A dermoscopic photograph of a skin lesion.
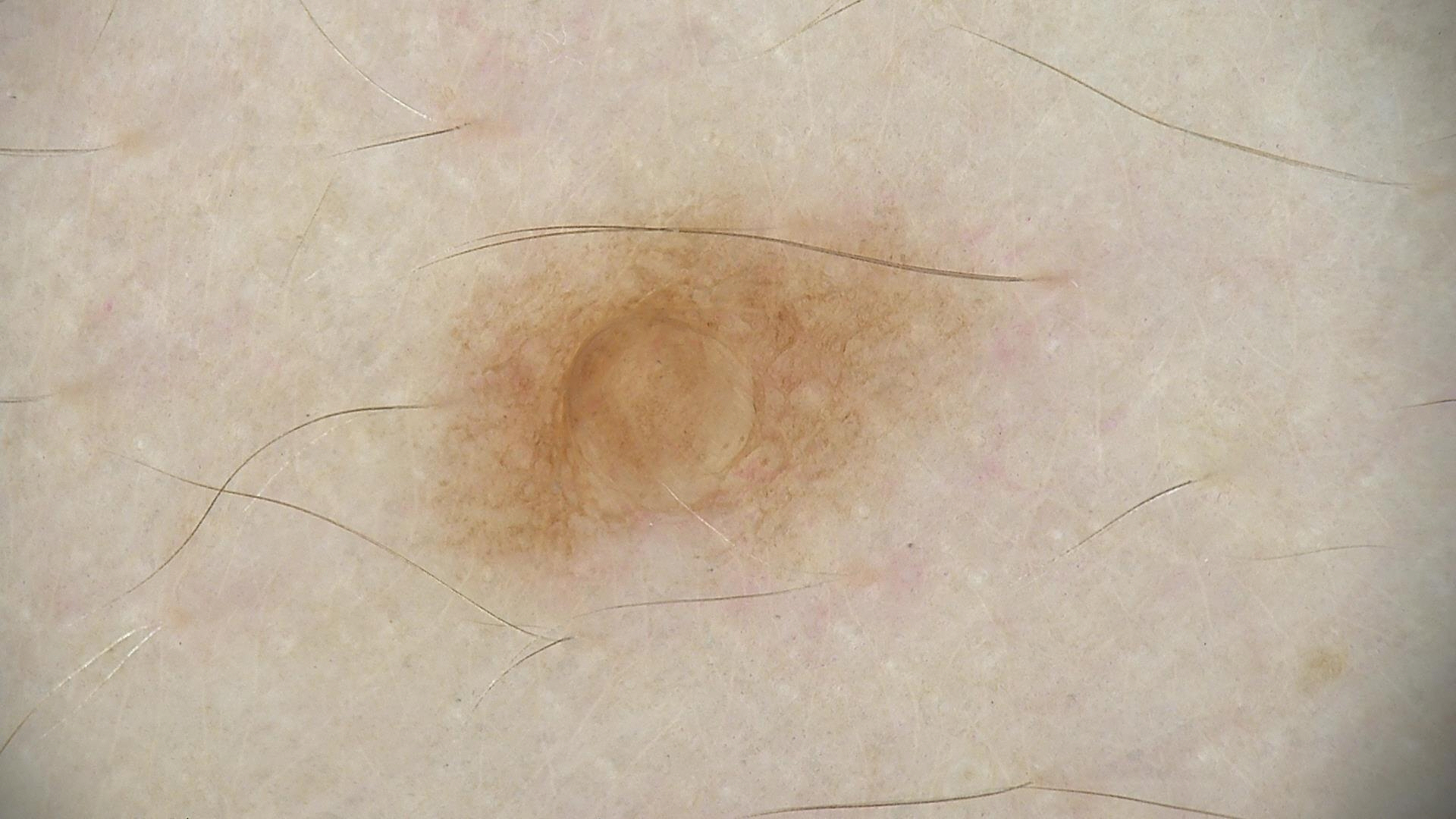The architecture is that of a banal lesion.
Diagnosed as a dermal nevus.